A dermoscopic photograph of a skin lesion.
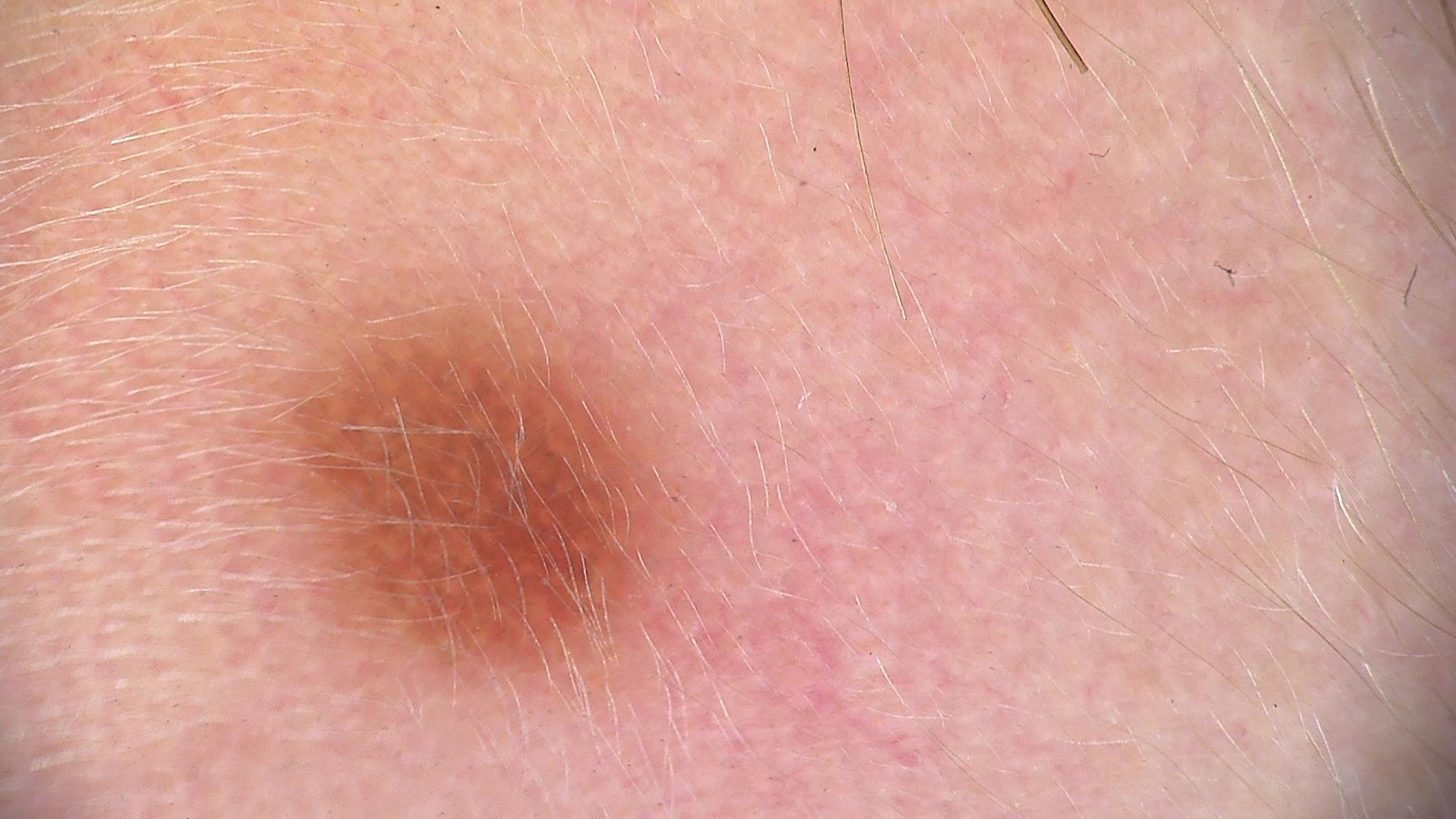Conclusion: Classified as a compound lesion — a Miescher nevus.